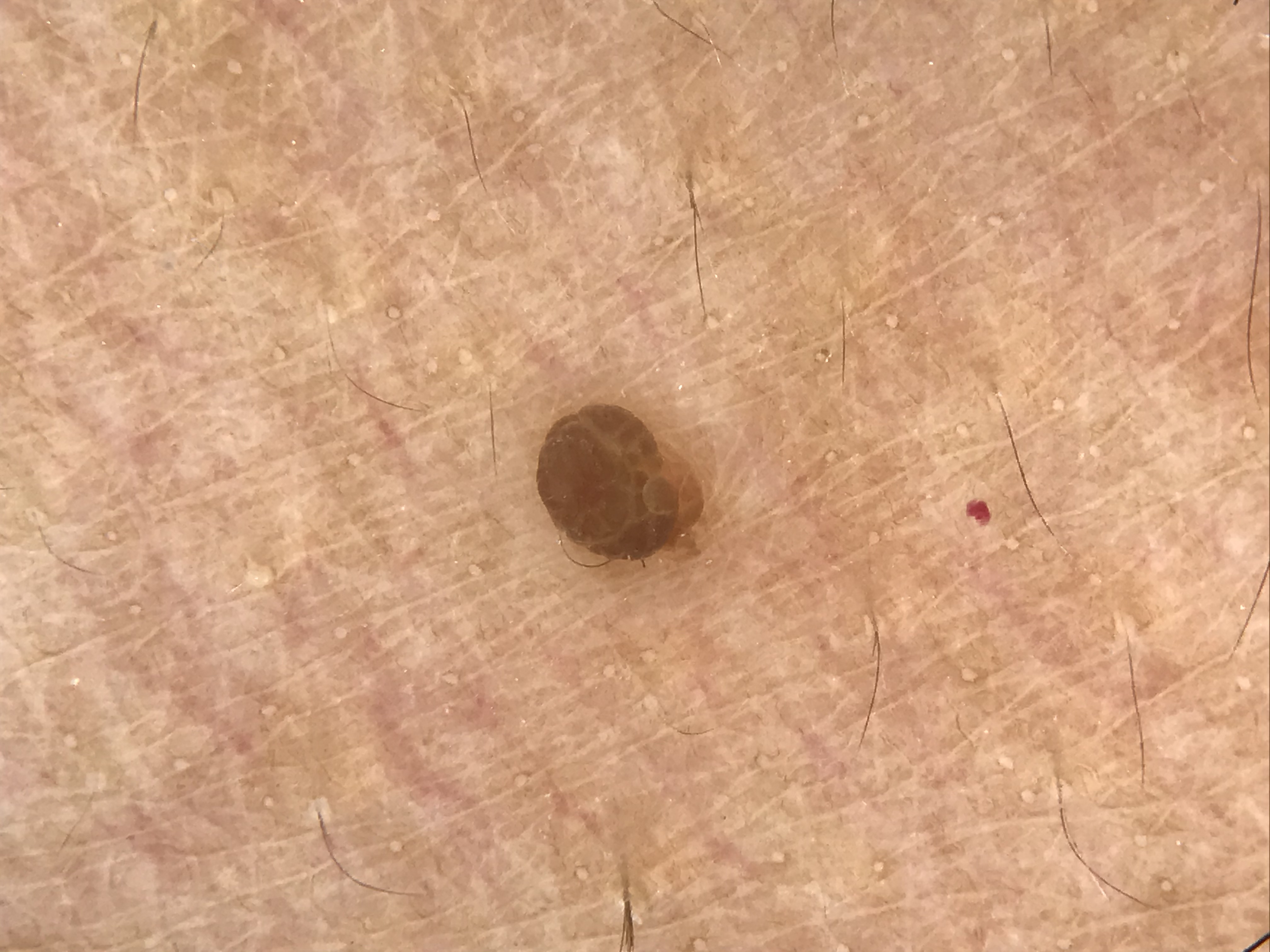Consistent with a banal lesion — a dermal nevus.